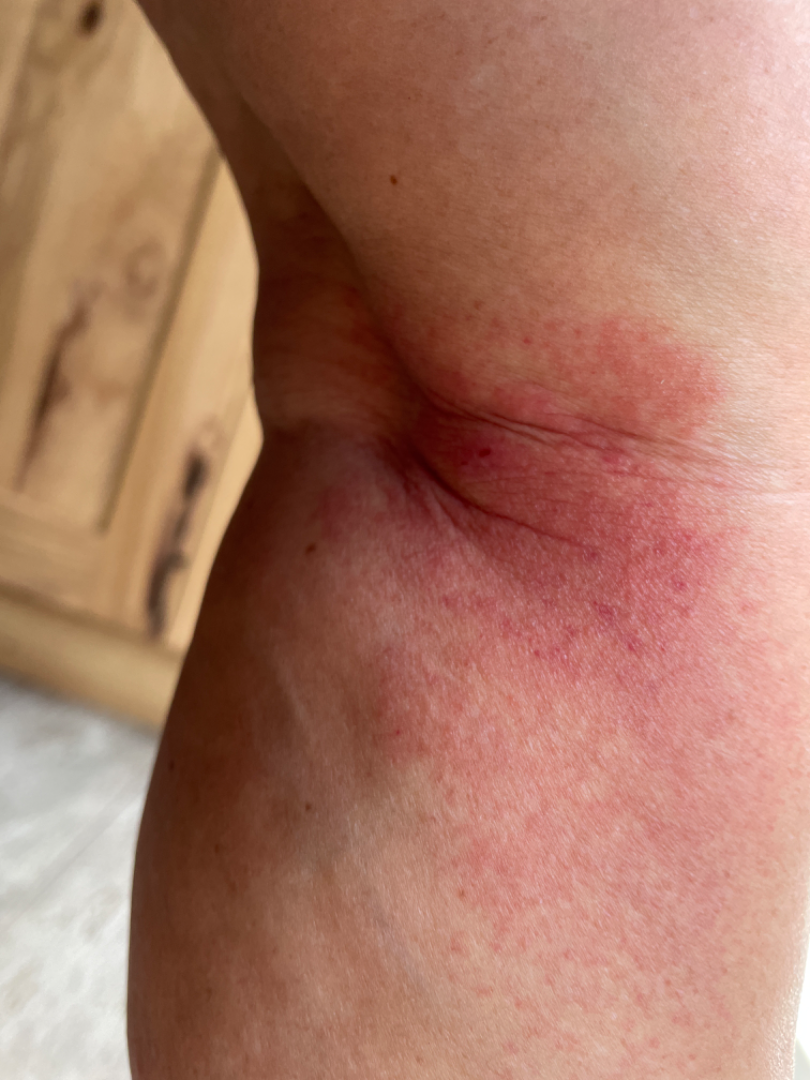Q: How does the lesion feel?
A: raised or bumpy
Q: What is the framing?
A: close-up
Q: How does the patient describe it?
A: a rash
Q: Where on the body?
A: leg
Q: What is the differential diagnosis?
A: the differential is split between Eczema, Allergic Contact Dermatitis and Irritant Contact Dermatitis